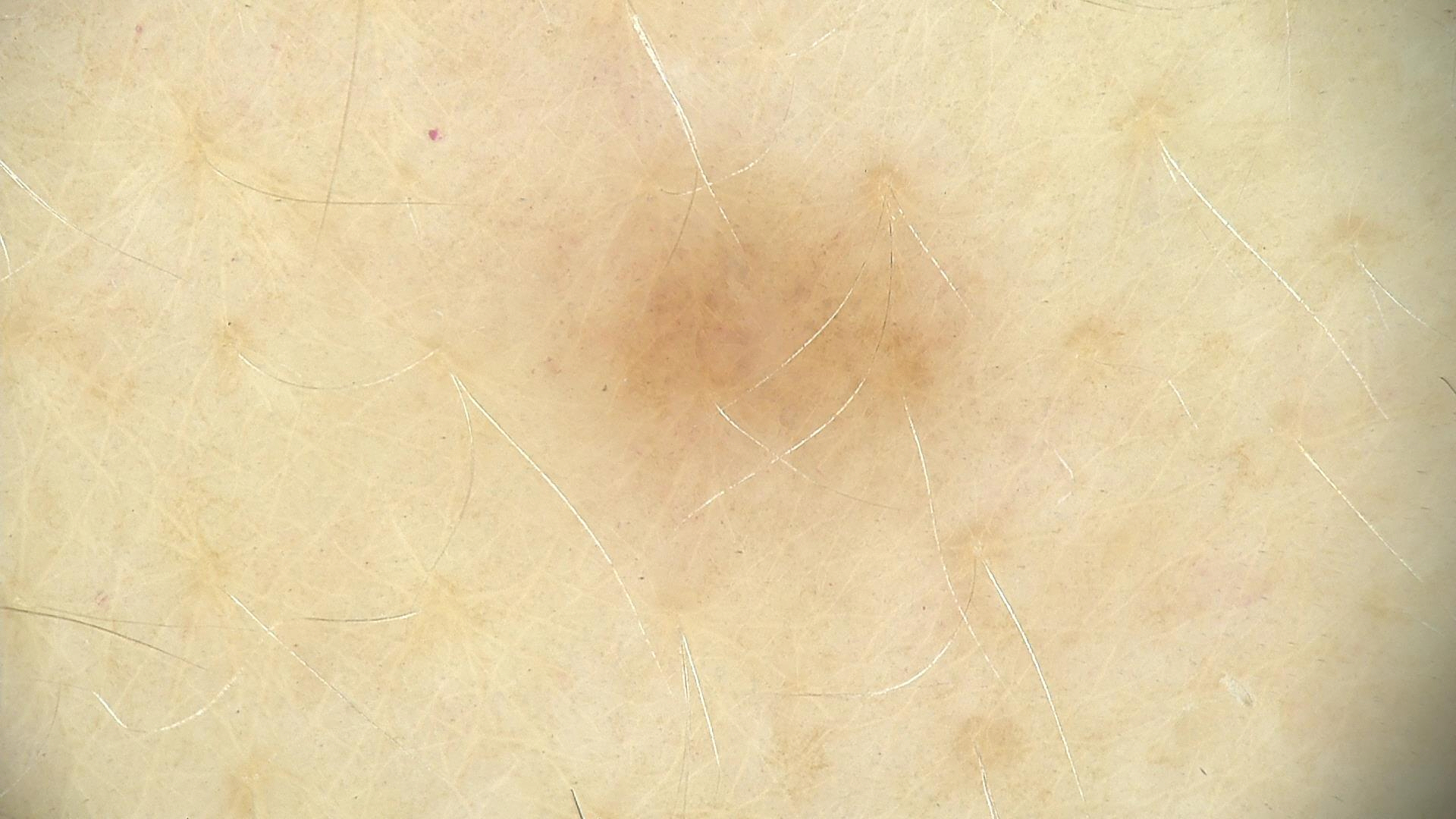Findings:
A dermoscopic photograph of a skin lesion.
Conclusion:
The diagnostic label was a dysplastic junctional nevus.